A clinical photograph showing a skin lesion:
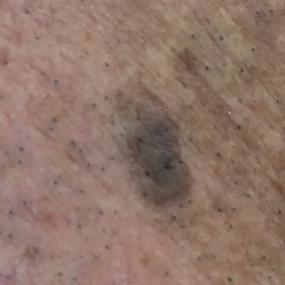Clinical context:
The lesion is located on the face. The patient describes that the lesion is elevated, but has not bled.
Conclusion:
Diagnosed by dermatologist consensus as a benign skin lesion — a seborrheic keratosis.